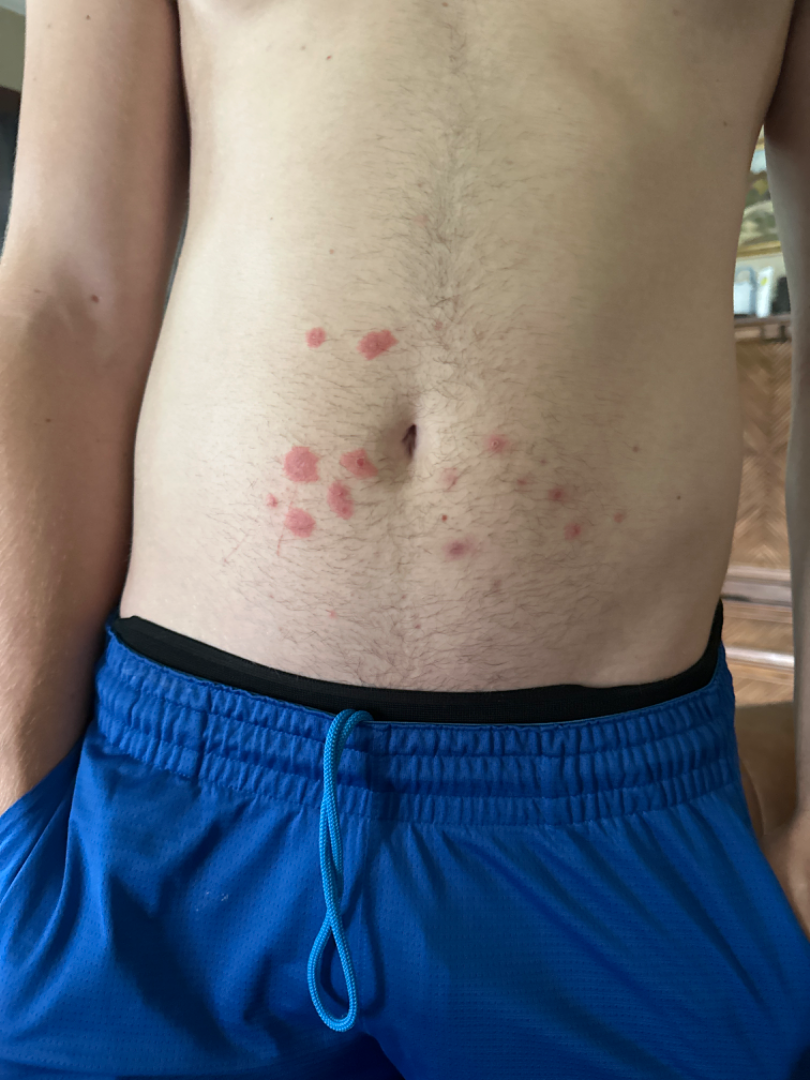site = front of the torso | texture = raised or bumpy | framing = at a distance | differential = the favored diagnosis is Insect Bite; also raised was Sweet syndrome.